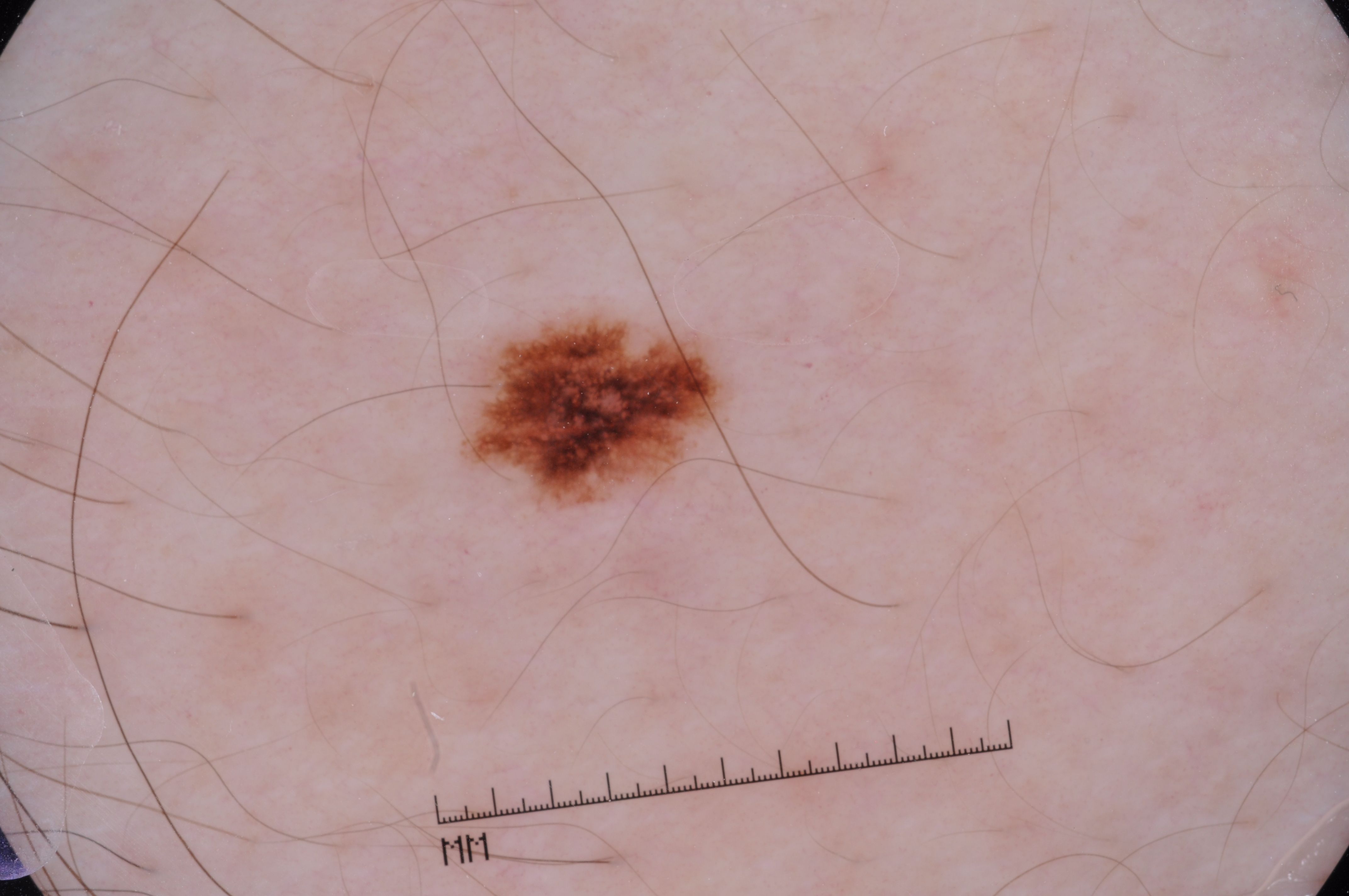imaging — dermatoscopic image of a skin lesion
patient — male, approximately 30 years of age
bounding box — x1=450, y1=306, x2=726, y2=517
size — small
features — pigment network; absent: streaks, milia-like cysts, and negative network
assessment — a melanocytic nevus